The photograph was taken at an angle; self-categorized by the patient as a rash; the contributor notes the condition has been present for less than one week; the lesion involves the arm; the lesion is associated with enlargement, bothersome appearance and itching; the contributor notes the lesion is raised or bumpy and fluid-filled — 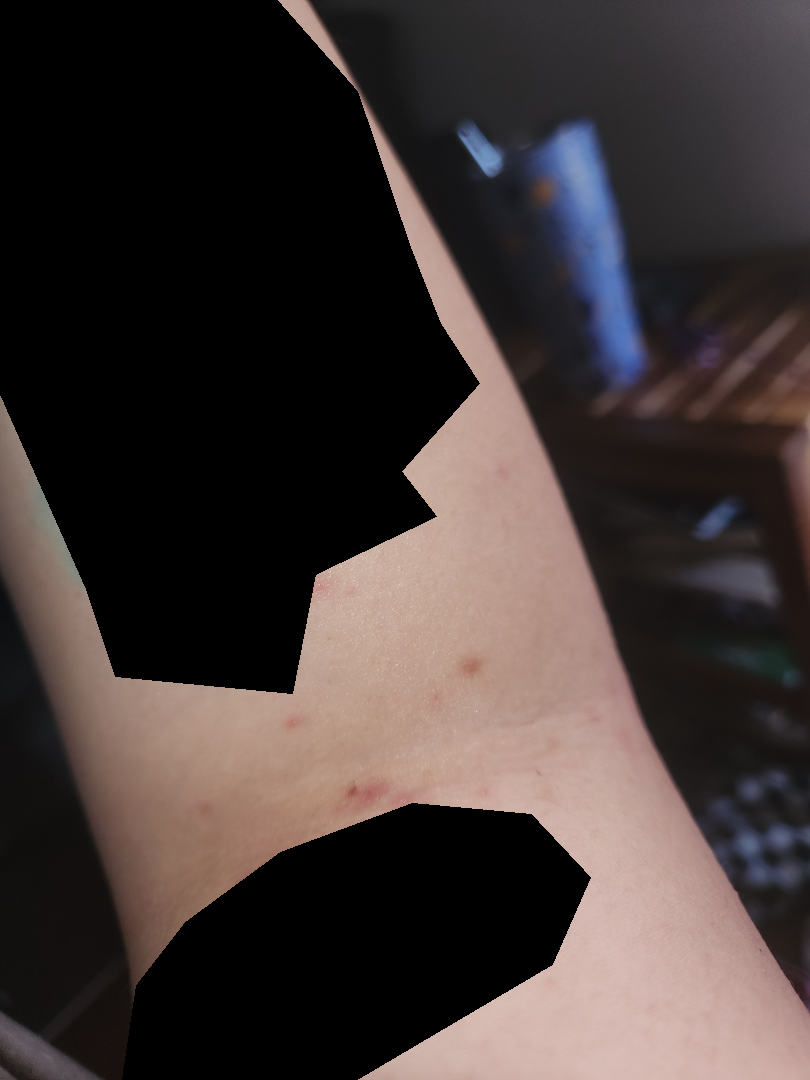On remote review of the image: consistent with Eczema.